Male patient, age 18–29. Located on the arm, leg and front of the torso. A close-up photograph — 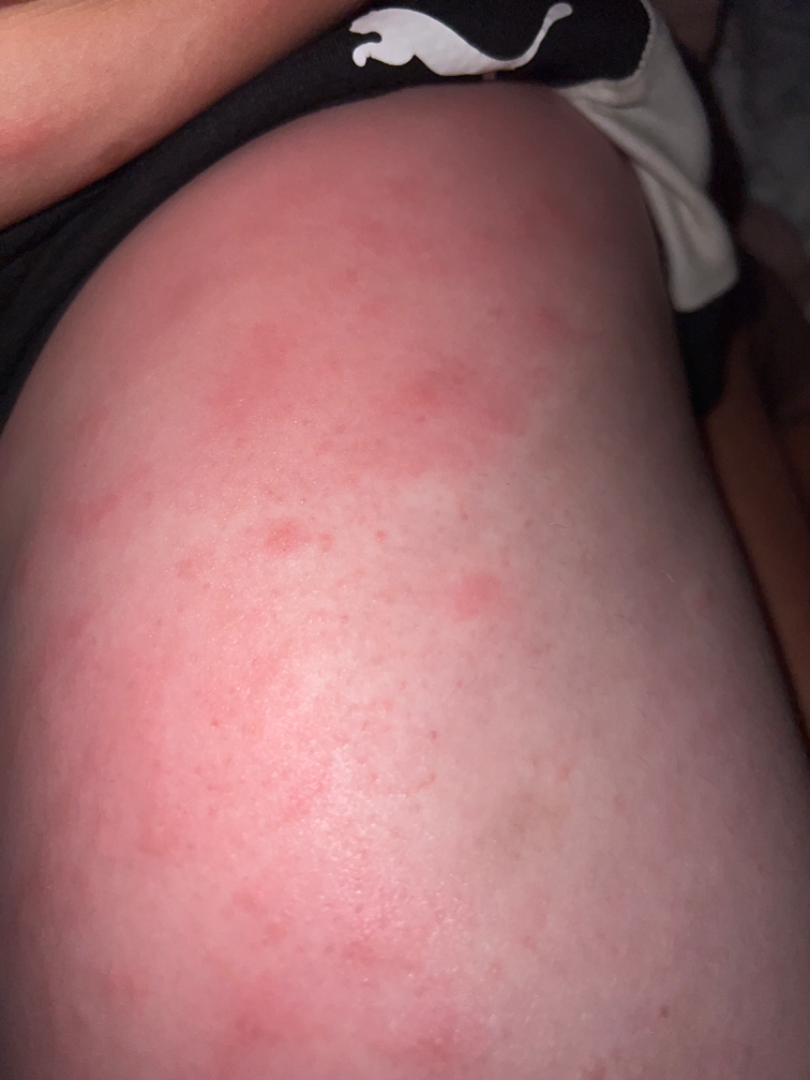Reviewed remotely by one dermatologist: Cellulitis and Allergic Contact Dermatitis were each considered, in no particular order.